A patient 28 years of age. A clinical close-up photograph of a skin lesion.
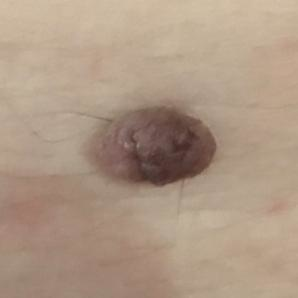<case>
  <diagnosis>
    <name>nevus</name>
    <code>NEV</code>
    <malignancy>benign</malignancy>
    <confirmation>clinical consensus</confirmation>
  </diagnosis>
</case>